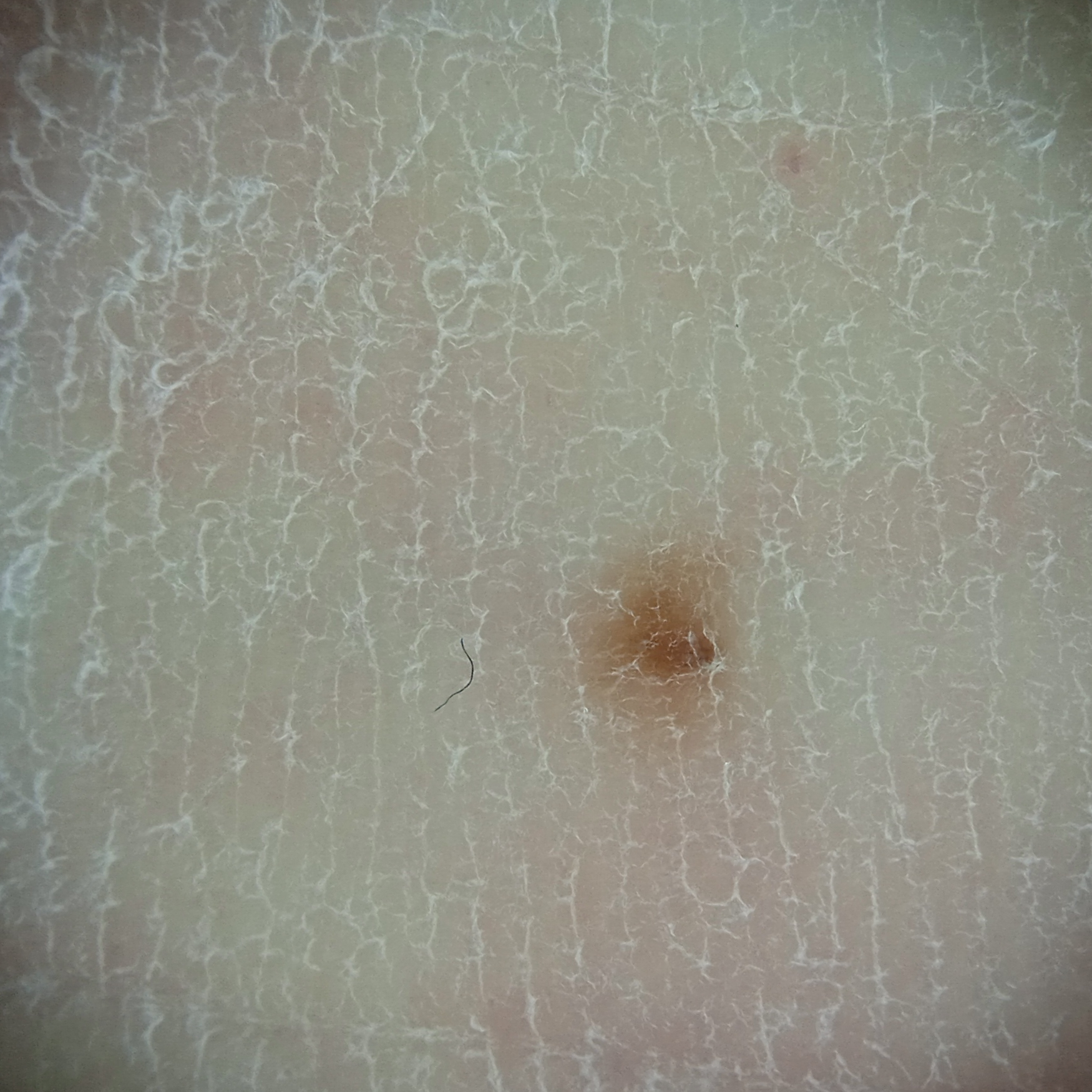mole_burden: a moderate number of melanocytic nevi
risk_factors:
  positive:
    - a personal history of cancer
referral: research study (no referral diagnosis)
patient:
  age: 54
  sex: male
sun_reaction: skin tans without first burning
image: dermoscopic image
lesion_location: a leg
lesion_size:
  diameter_mm: 2.2
diagnosis:
  name: melanocytic nevus
  malignancy: benign